The patient is skin type II · a dermoscopic photograph of a skin lesion · a female patient aged approximately 55.
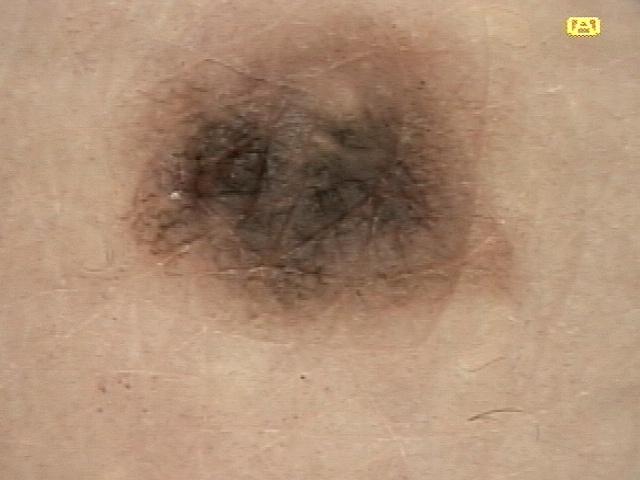diagnosis = Nevus (biopsy-proven).